The arm and leg are involved; the contributor is a female aged 18–29; the photograph is a close-up of the affected area — 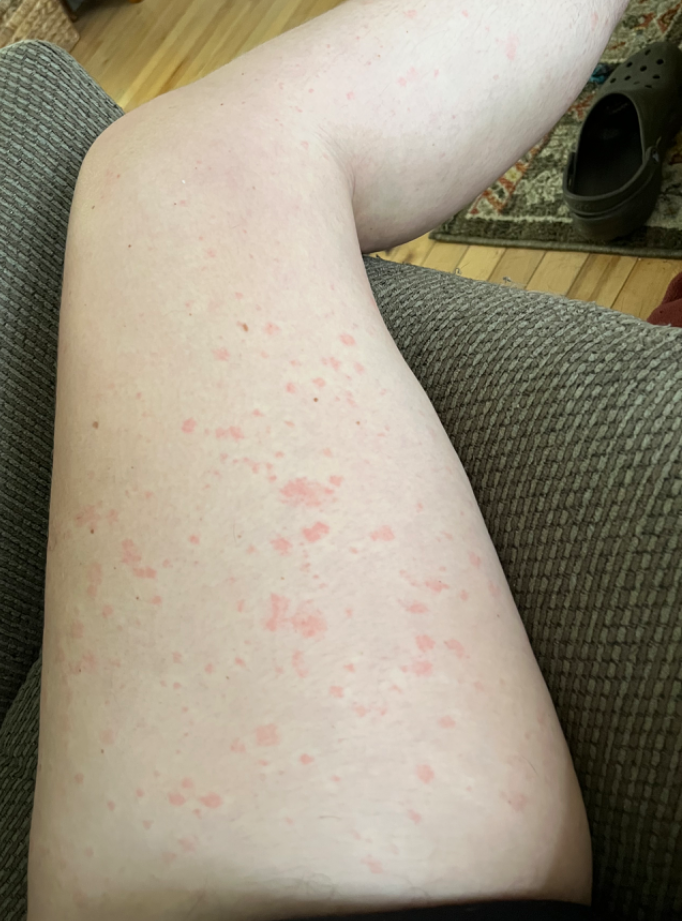symptom duration: less than one week; self-categorized as: a rash; diagnostic considerations: most consistent with Urticaria.